A dermoscopic image of a skin lesion:
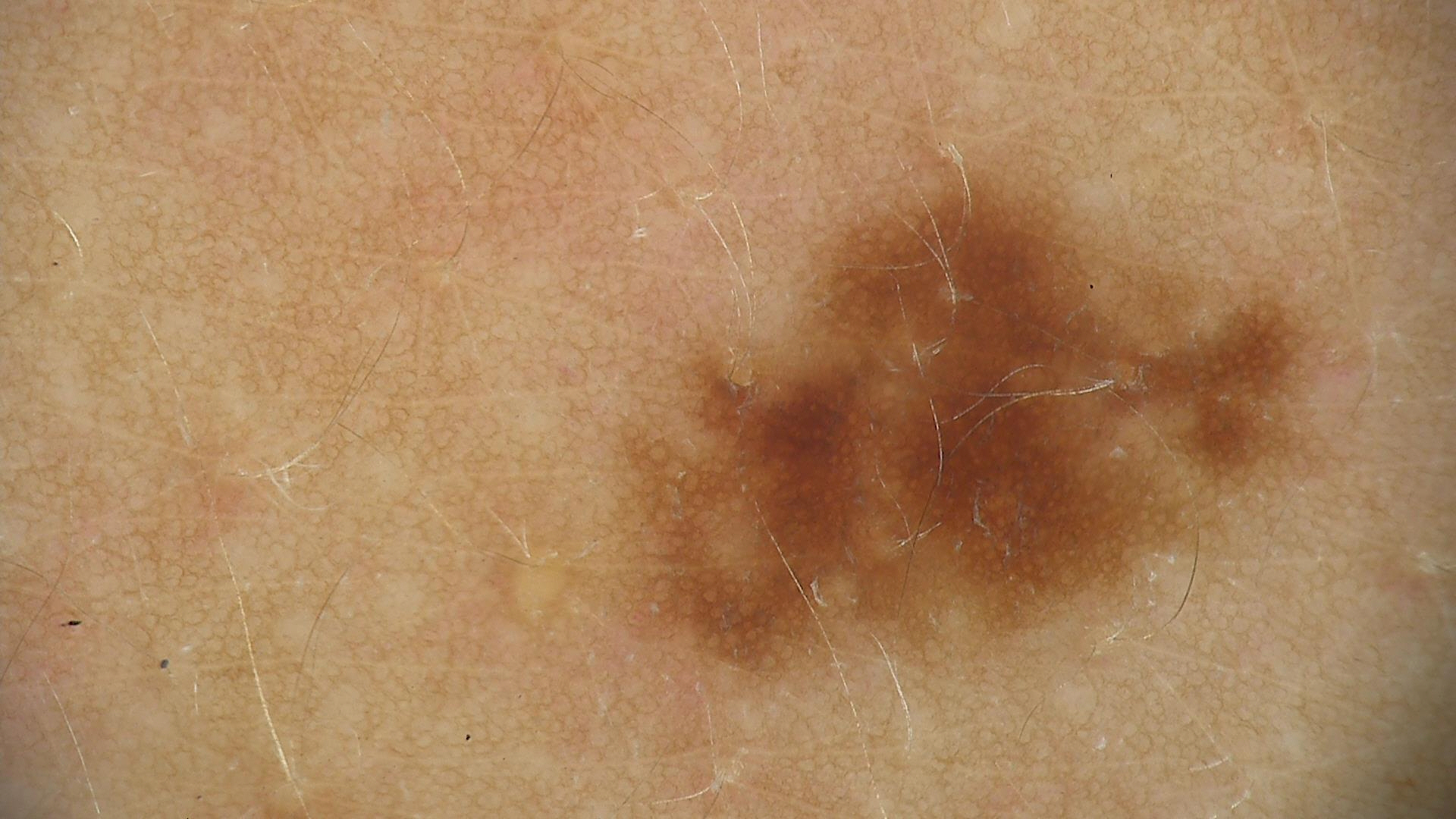| key | value |
|---|---|
| diagnostic label | dysplastic junctional nevus (expert consensus) |